The photo was captured at a distance · the palm is involved · the patient reported no systemic symptoms · the patient described the issue as a rash · the contributor is 40–49, female · the lesion is described as raised or bumpy · symptoms reported: itching · the patient indicates the condition has been present for one to four weeks:
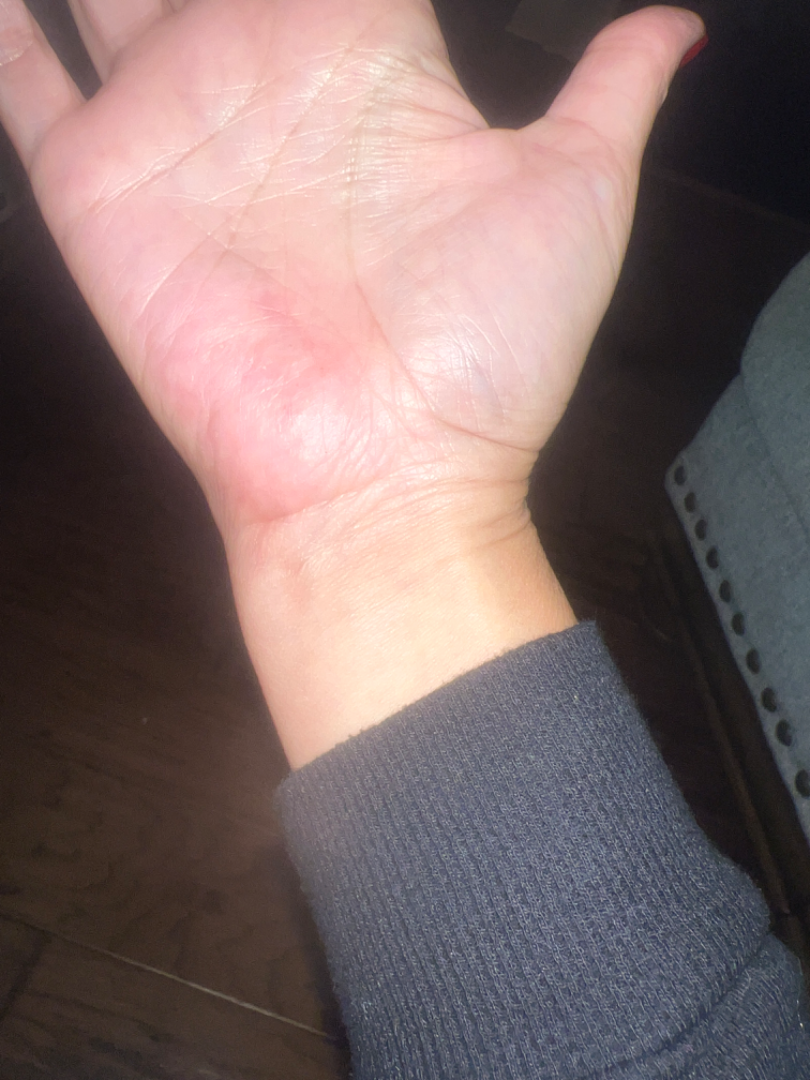Most likely Eczema; also consider Allergic Contact Dermatitis.